A clinical photograph showing a skin lesion; recorded as skin type II; a male subject 77 years old; the chart records prior skin cancer (patient or family):
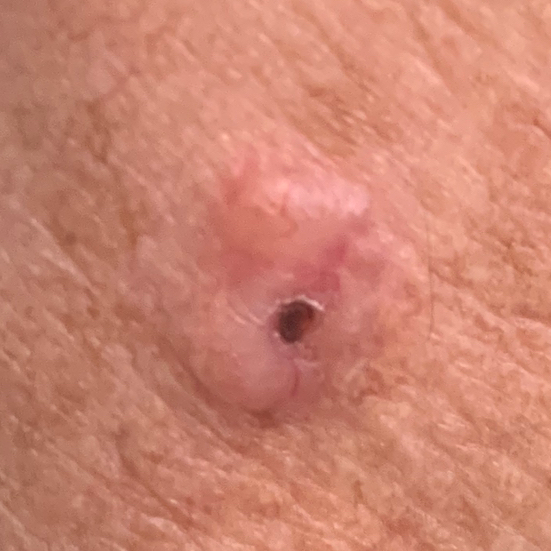The lesion is roughly 10 by 9 mm. Per patient report, the lesion has grown, has changed, has bled, is elevated, and itches, but does not hurt. Histopathological examination showed an actinic keratosis.